A dermoscopic image of a skin lesion:
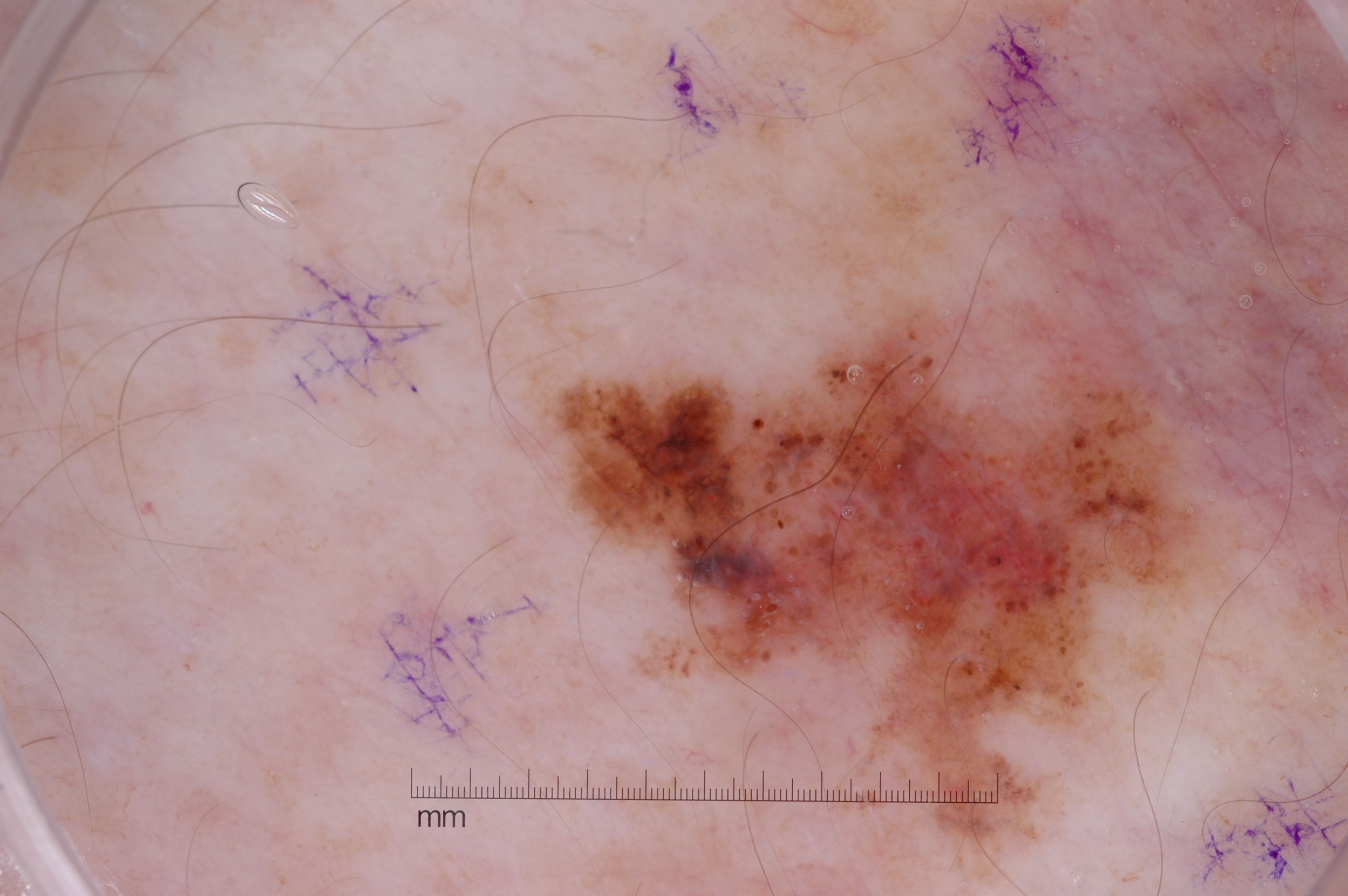  lesion_location:
    bbox_xyxy:
      - 541
      - 274
      - 1200
      - 877
  diagnosis:
    name: melanoma
    malignancy: malignant
    lineage: melanocytic
    provenance: histopathology